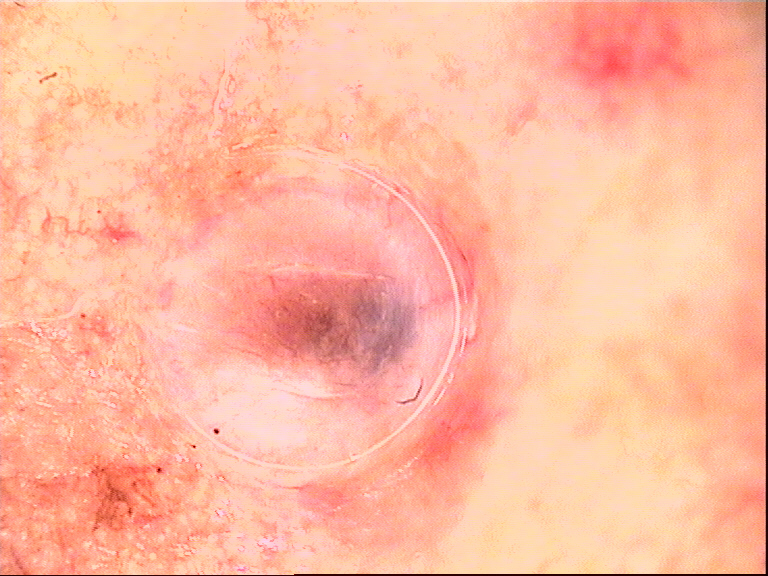Q: What is the diagnosis?
A: dermal nevus (expert consensus)